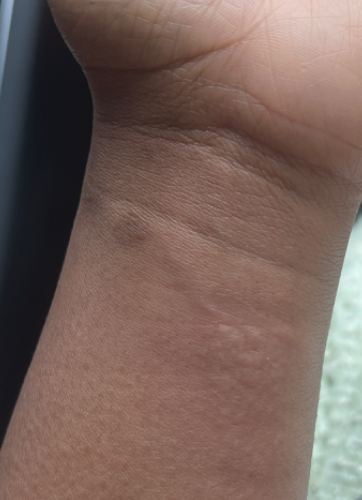Case summary:
– self-categorized as — a rash
– location — arm and leg
– photo taken — at an angle
– symptoms — bleeding, bothersome appearance and itching
– described texture — flat and raised or bumpy
– assessment — consistent with Eczema